The photo was captured at an angle — 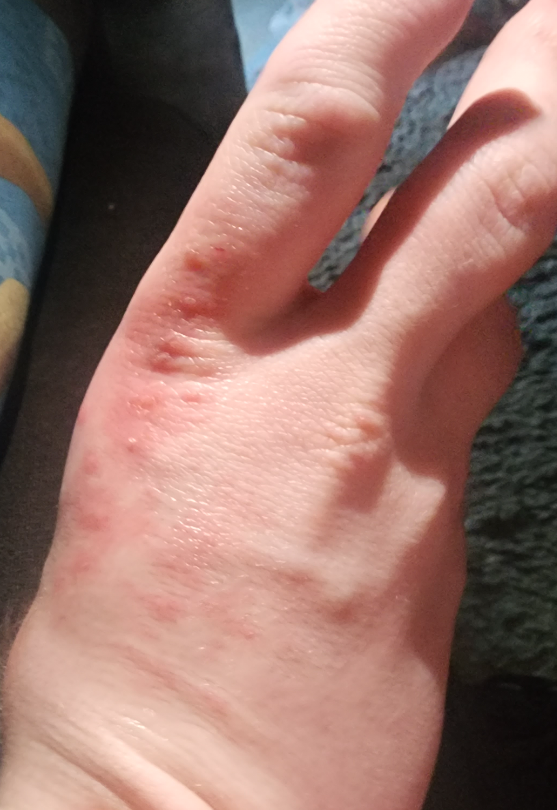On photographic review: in keeping with Eczema.